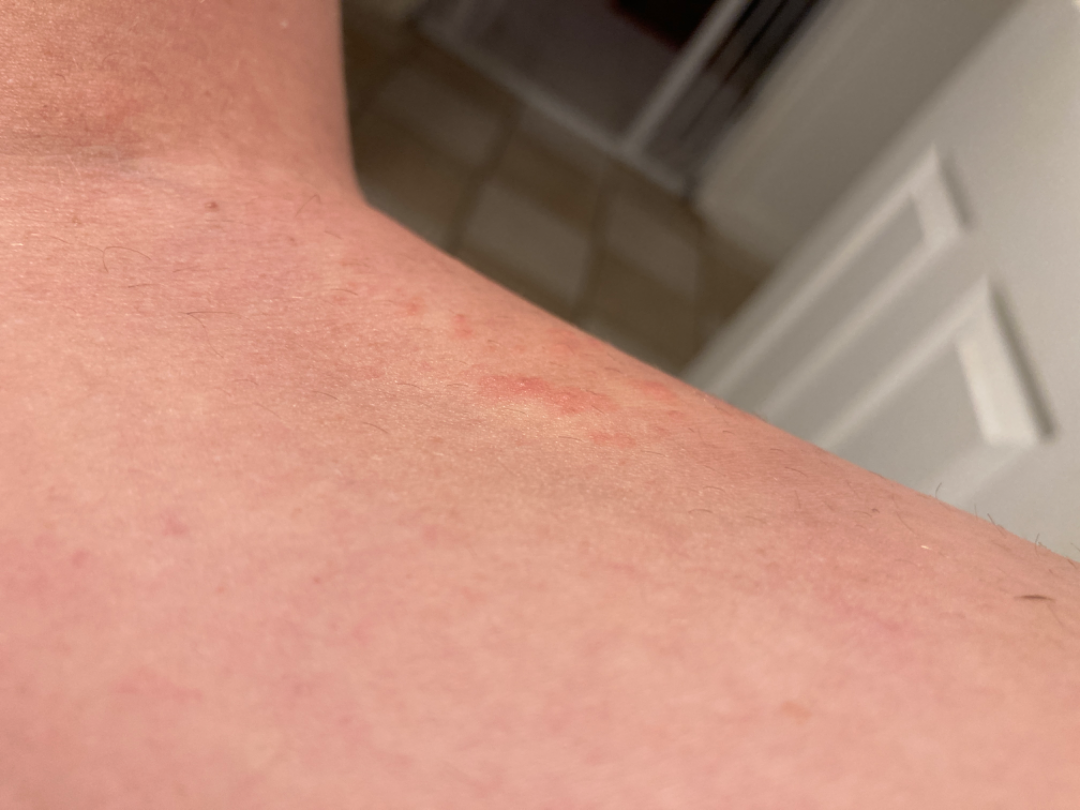Q: Duration?
A: about one day
Q: Patient demographics?
A: female, age 30–39
Q: Image view?
A: at an angle
Q: What is the affected area?
A: leg
Q: How does the lesion feel?
A: raised or bumpy
Q: What is the differential diagnosis?
A: the leading consideration is Hypersensitivity; an alternative is Eczema